The patient describes having few moles overall. A dermoscopic image of a skin lesion. The patient reports a personal history of cancer. The patient says their skin tans without first burning. A female patient age 84. Collected as part of a research study, without a referral diagnosis: 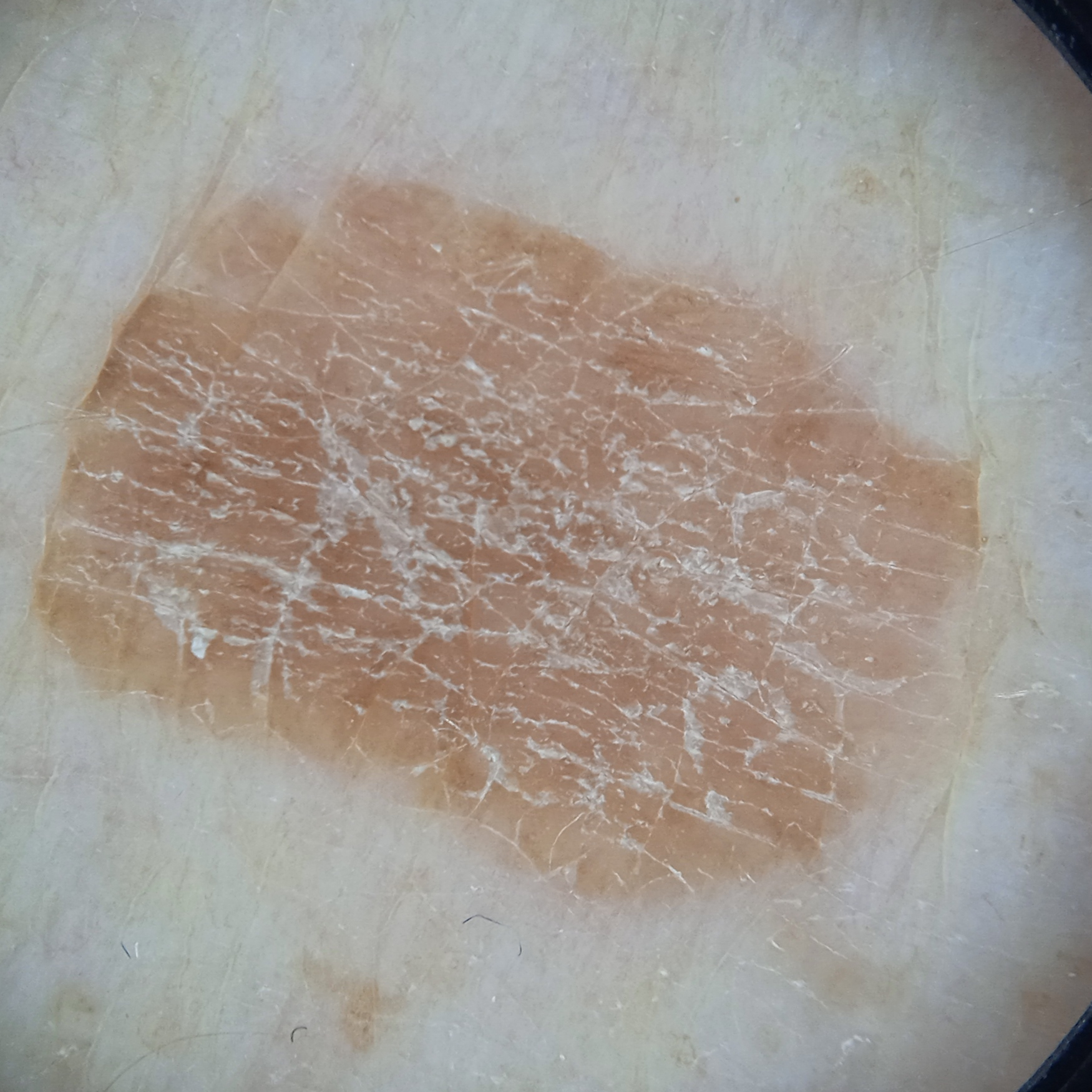body site — an arm | diameter — 11.2 mm | diagnosis — seborrheic keratosis (dermatologist consensus).